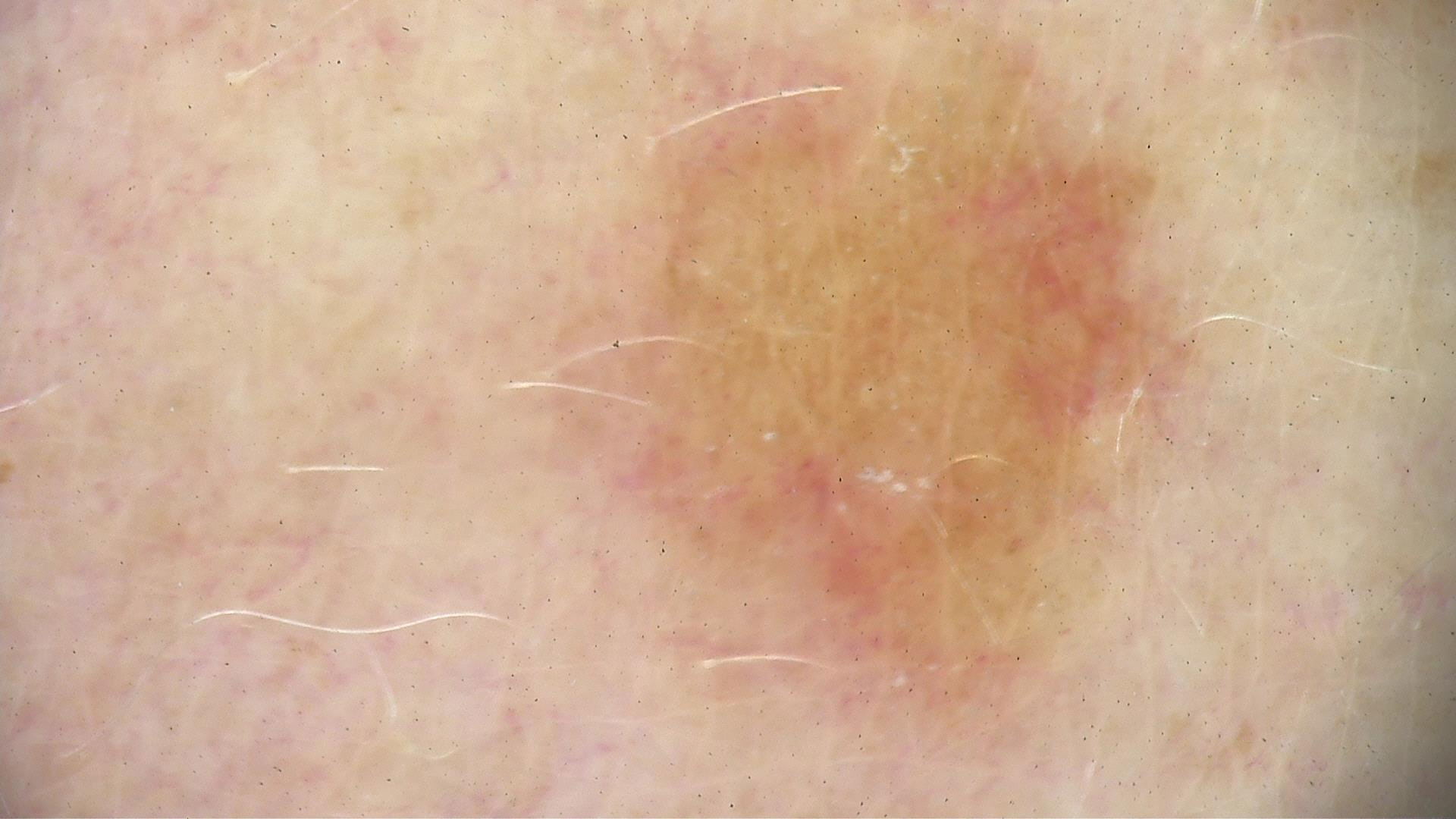Classified as a junctional nevus.